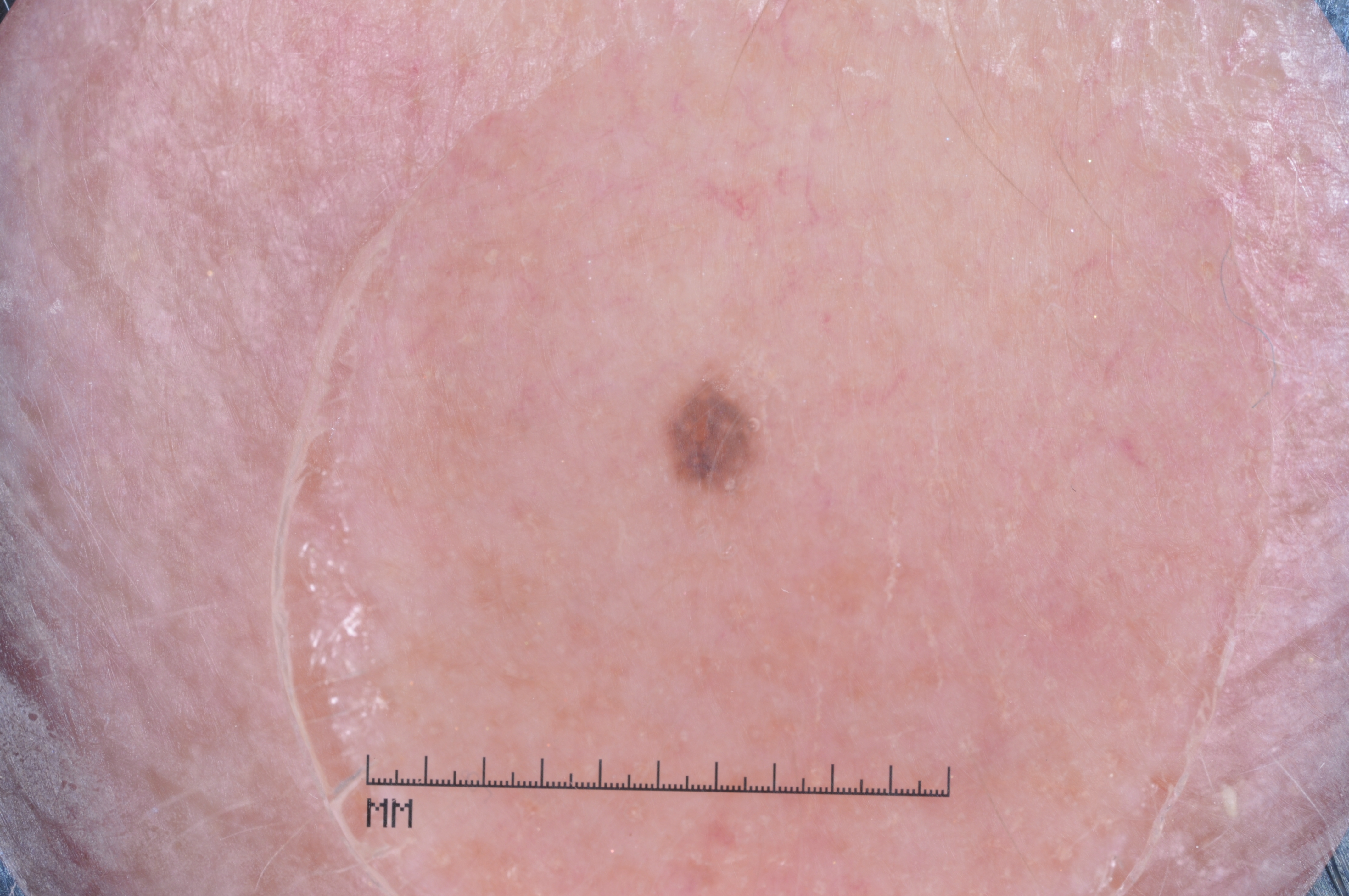Q: What is the imaging modality?
A: dermatoscopic image of a skin lesion
Q: Which assessed dermoscopic features were absent?
A: milia-like cysts, pigment network, negative network, and streaks
Q: Where is the lesion in the image?
A: bbox(660, 371, 764, 525)
Q: What is this lesion?
A: a melanocytic nevus